A dermoscopy image of a single skin lesion, a female patient about 50 years old — 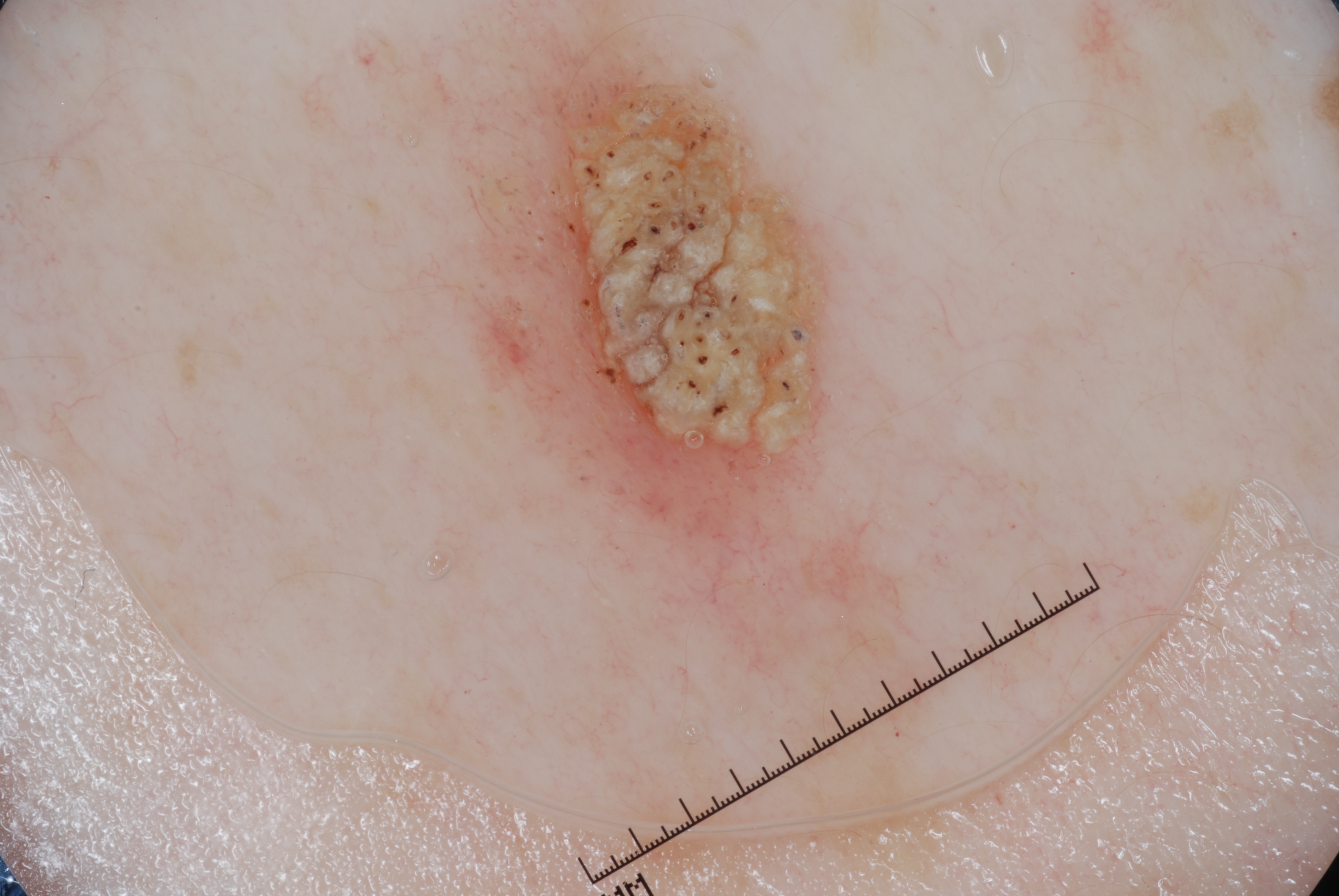Dermoscopically, the lesion shows milia-like cysts.
As (left, top, right, bottom), the lesion spans 390 0 1193 895.
The lesion covers approximately 22% of the dermoscopic field.
Part of the lesion extends beyond the imaged area.
The diagnostic assessment was a seborrheic keratosis, a lesion of keratinocytic origin.